The affected area is the back of the hand, palm and arm; female patient, age 50–59; the photograph was taken at an angle:
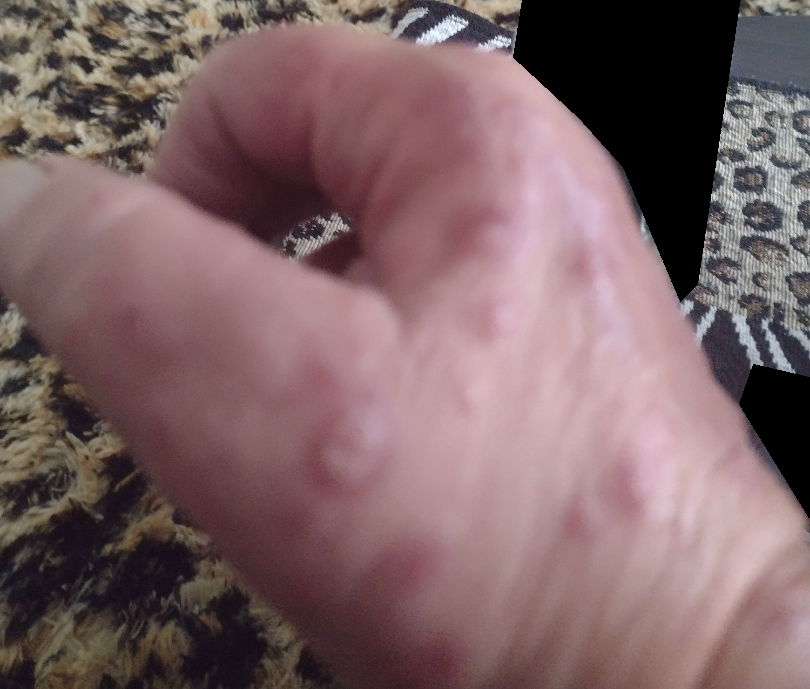{
  "differential": {
    "leading": [
      "Syphilis"
    ],
    "considered": [
      "Viral Exanthem",
      "Erythema multiforme"
    ]
  }
}